Located on the leg, this image was taken at a distance — 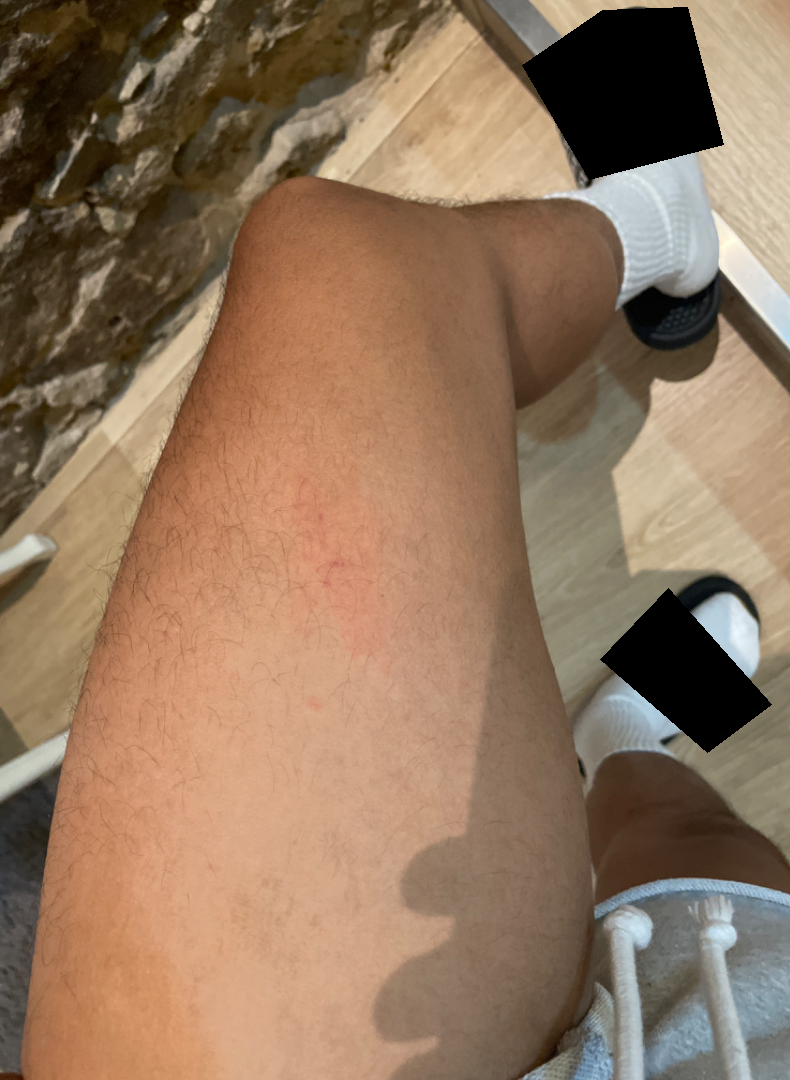Impression: The image was not sufficient for the reviewer to characterize the skin condition.